The patient describes having few moles overall; the referring clinician suspected basal cell carcinoma; dermoscopy of a skin lesion; a female subject 60 years old; the patient says their skin tans without first burning: 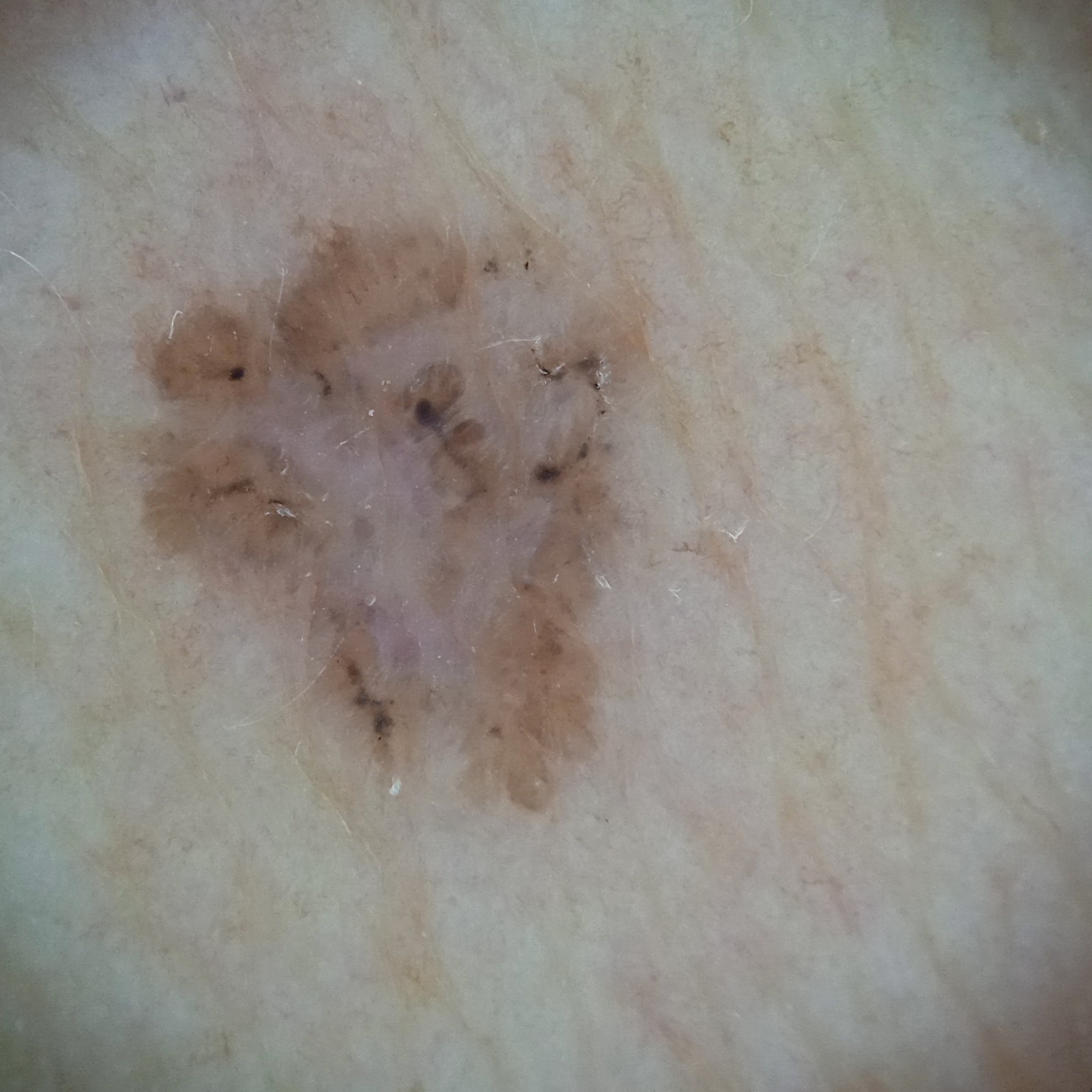anatomic site: the torso
diameter: 7.2 mm
assessment: basal cell carcinoma (dermatologist consensus)